The lesion involves the arm, back of the torso, front of the torso, head or neck, leg, palm and back of the hand; close-up view; the contributor is 70–79, male.
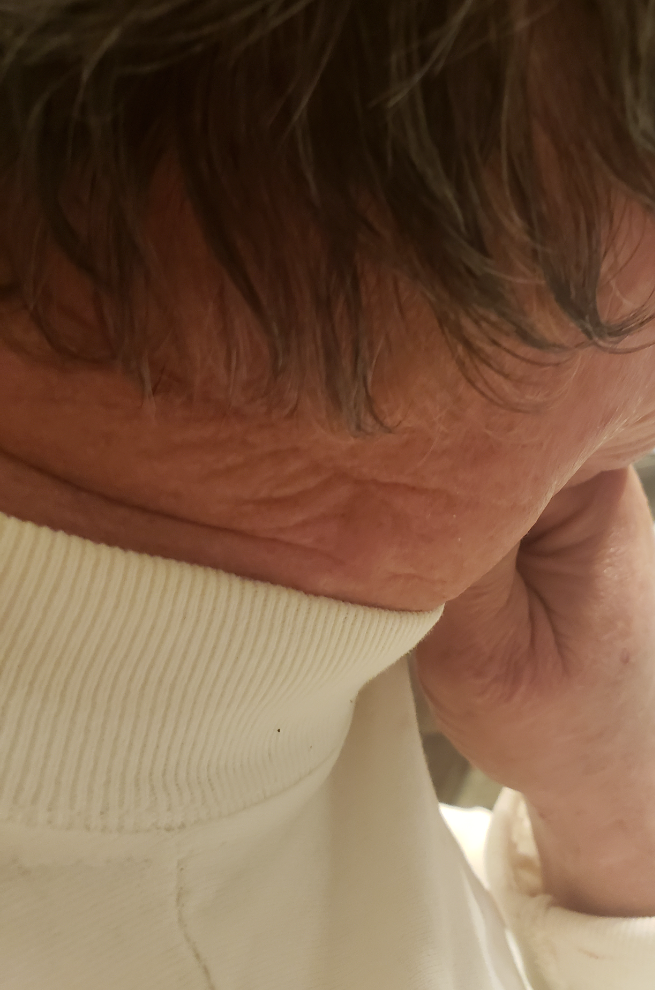Notes:
– diagnostic considerations — the primary impression is Seborrheic Dermatitis; an alternative is Psoriasis; the differential also includes Allergic Contact Dermatitis